A dermoscopy image of a single skin lesion:
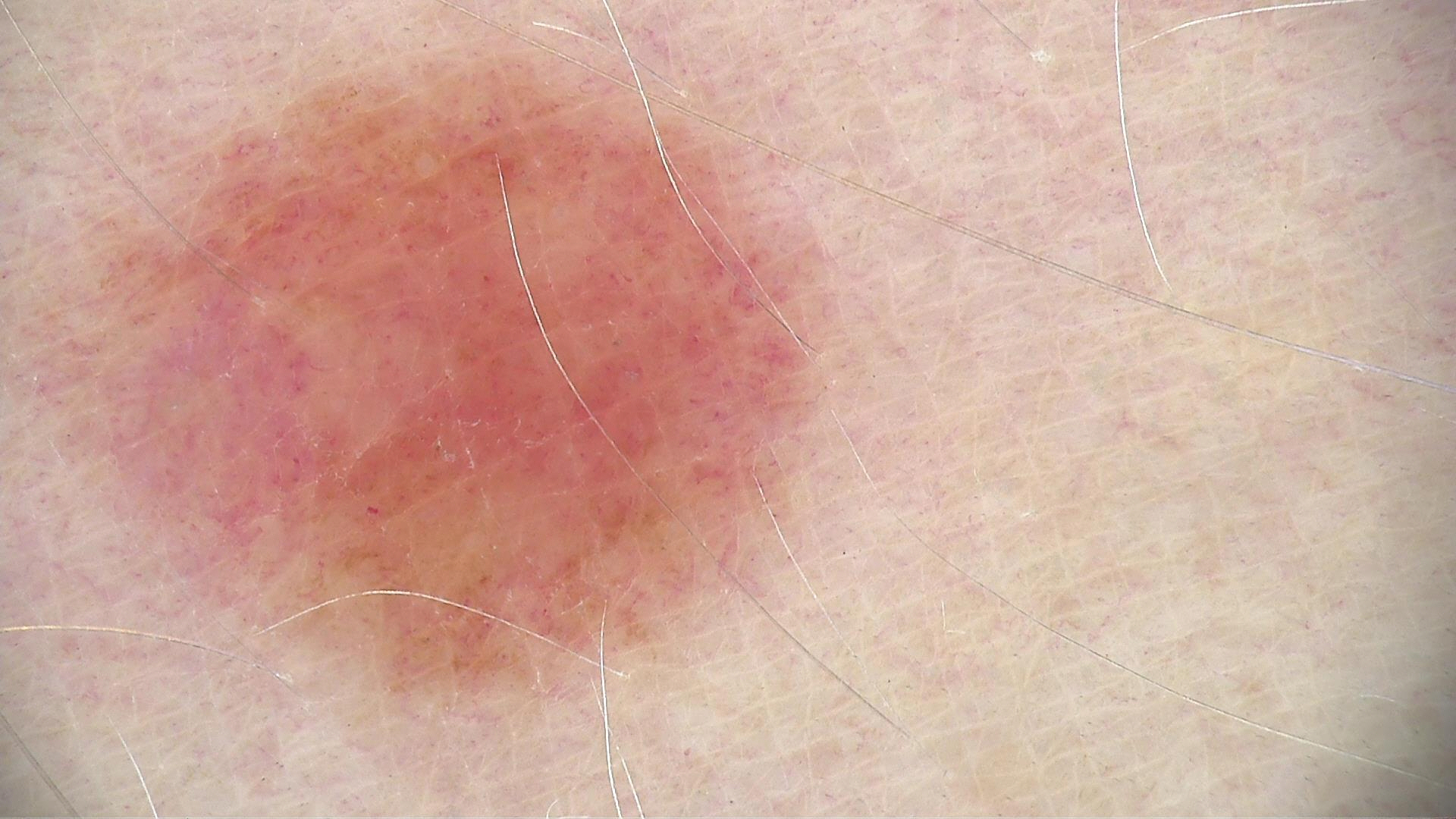Q: What was the diagnostic impression?
A: dysplastic junctional nevus (expert consensus)